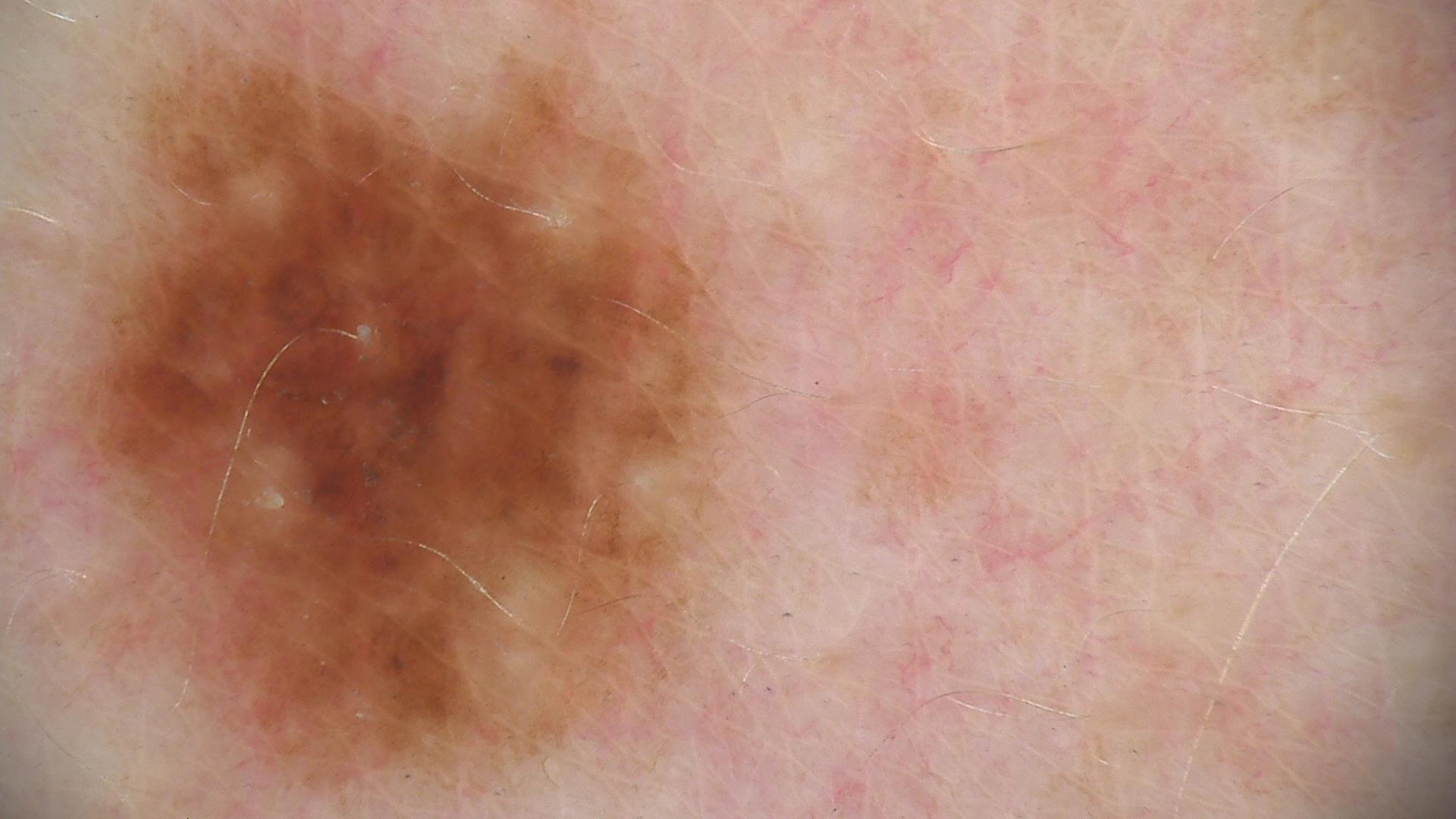image type: dermatoscopy
label: dysplastic junctional nevus (expert consensus)